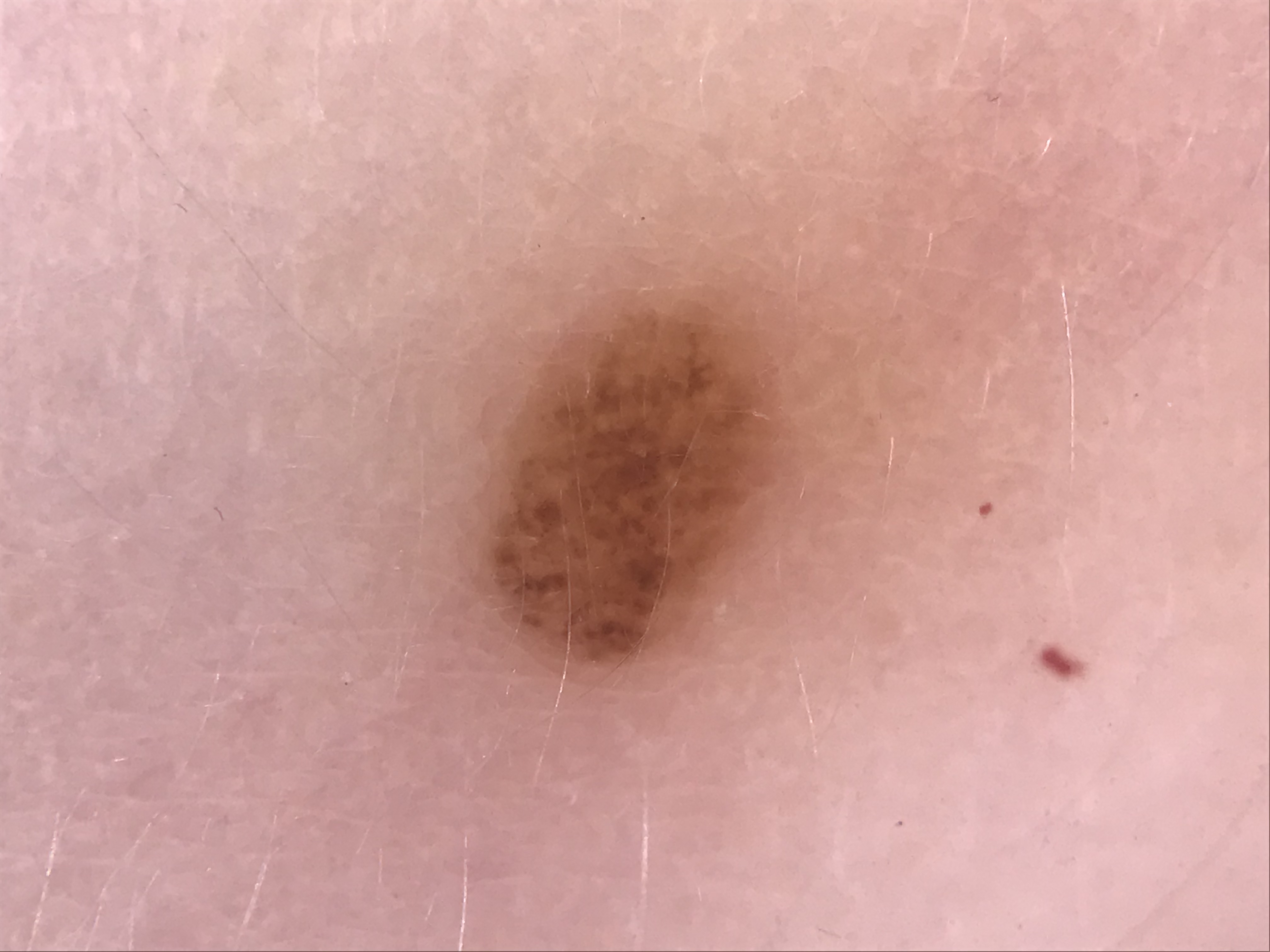Labeled as a banal lesion — a compound nevus.